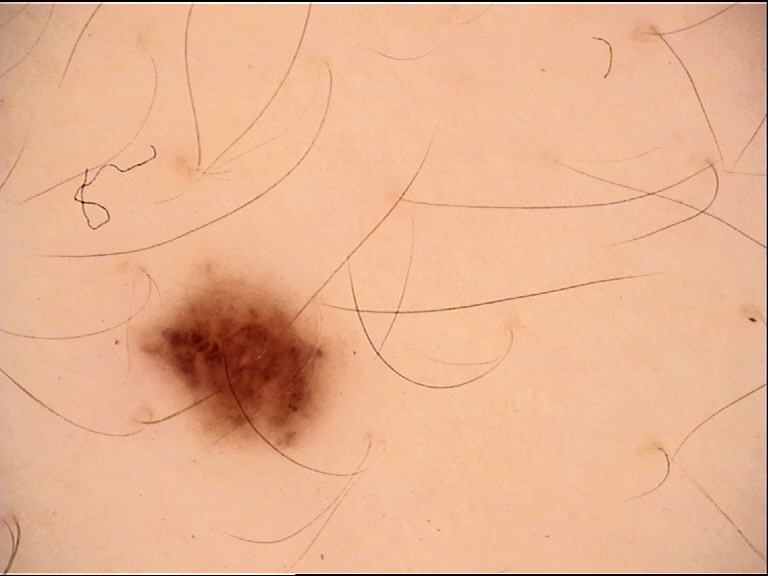imaging = dermatoscopy, category = banal, assessment = junctional nevus (expert consensus).